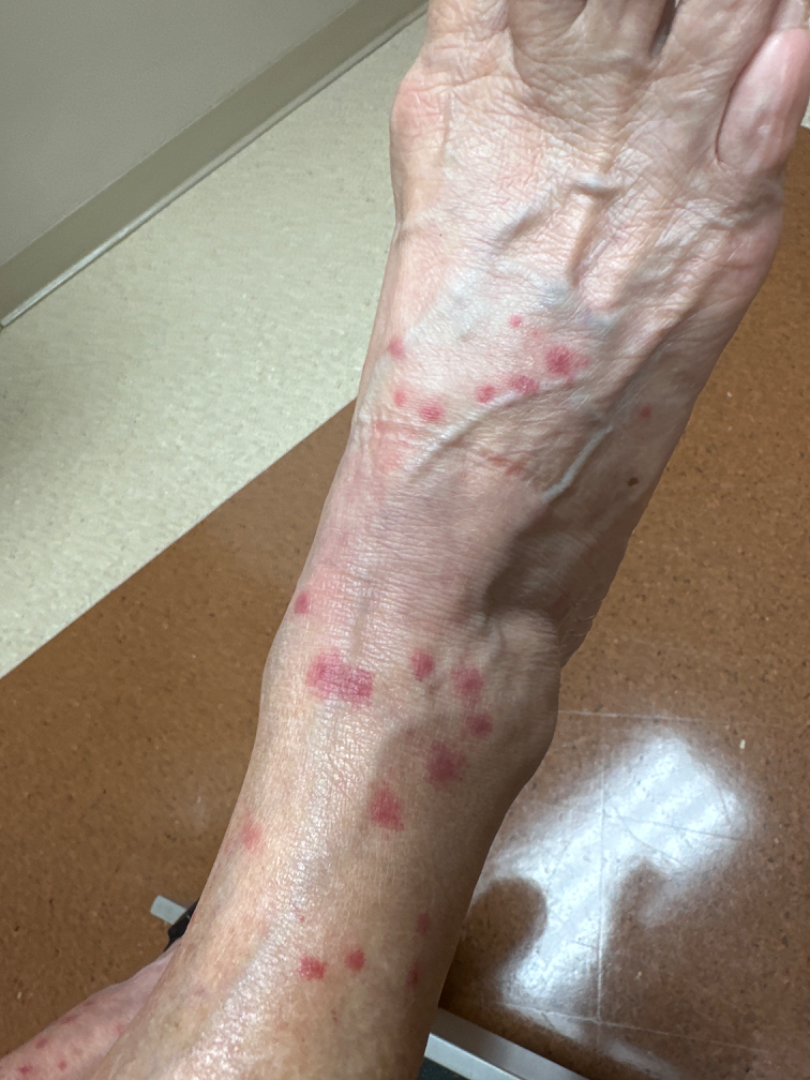The photograph is a close-up of the affected area. The contributor is female. The lesion involves the leg and top or side of the foot. On photographic review by a dermatologist, the differential is split between Insect Bite and Leukocytoclastic Vasculitis.